An image taken at an angle: 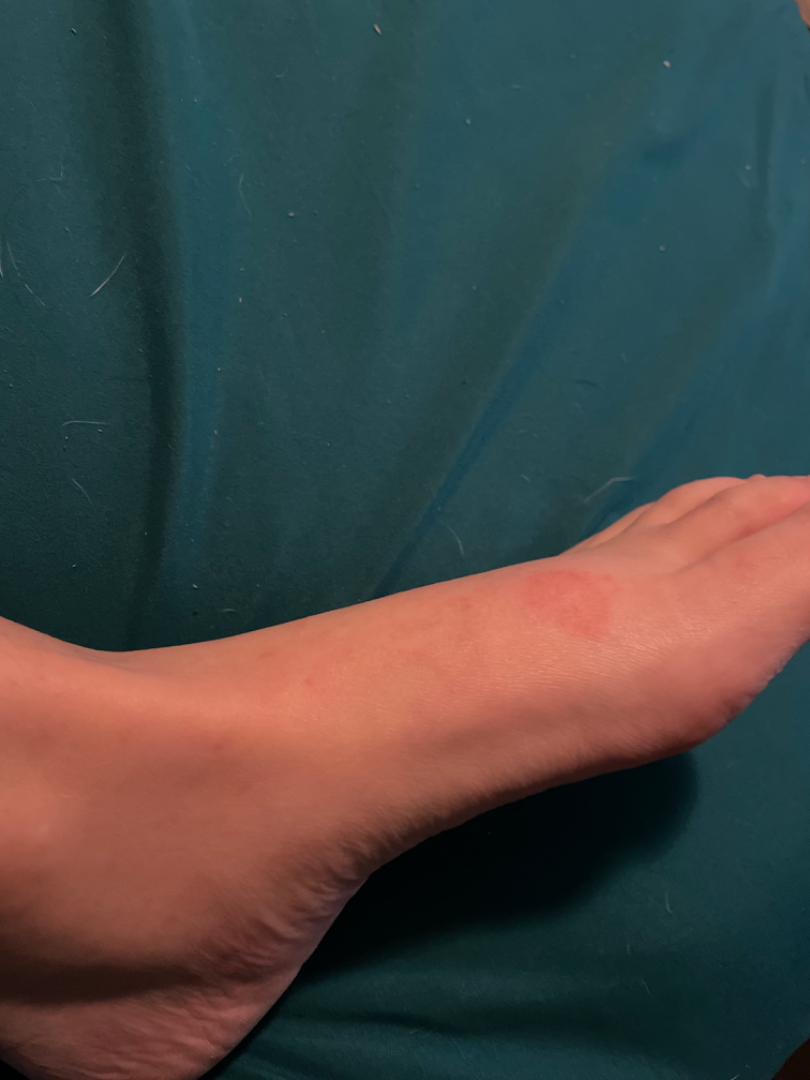Q: What conditions are considered?
A: Lichen Simplex Chronicus (considered); Allergic Contact Dermatitis (considered); Irritant Contact Dermatitis (considered)